A dermoscopic view of a skin lesion — 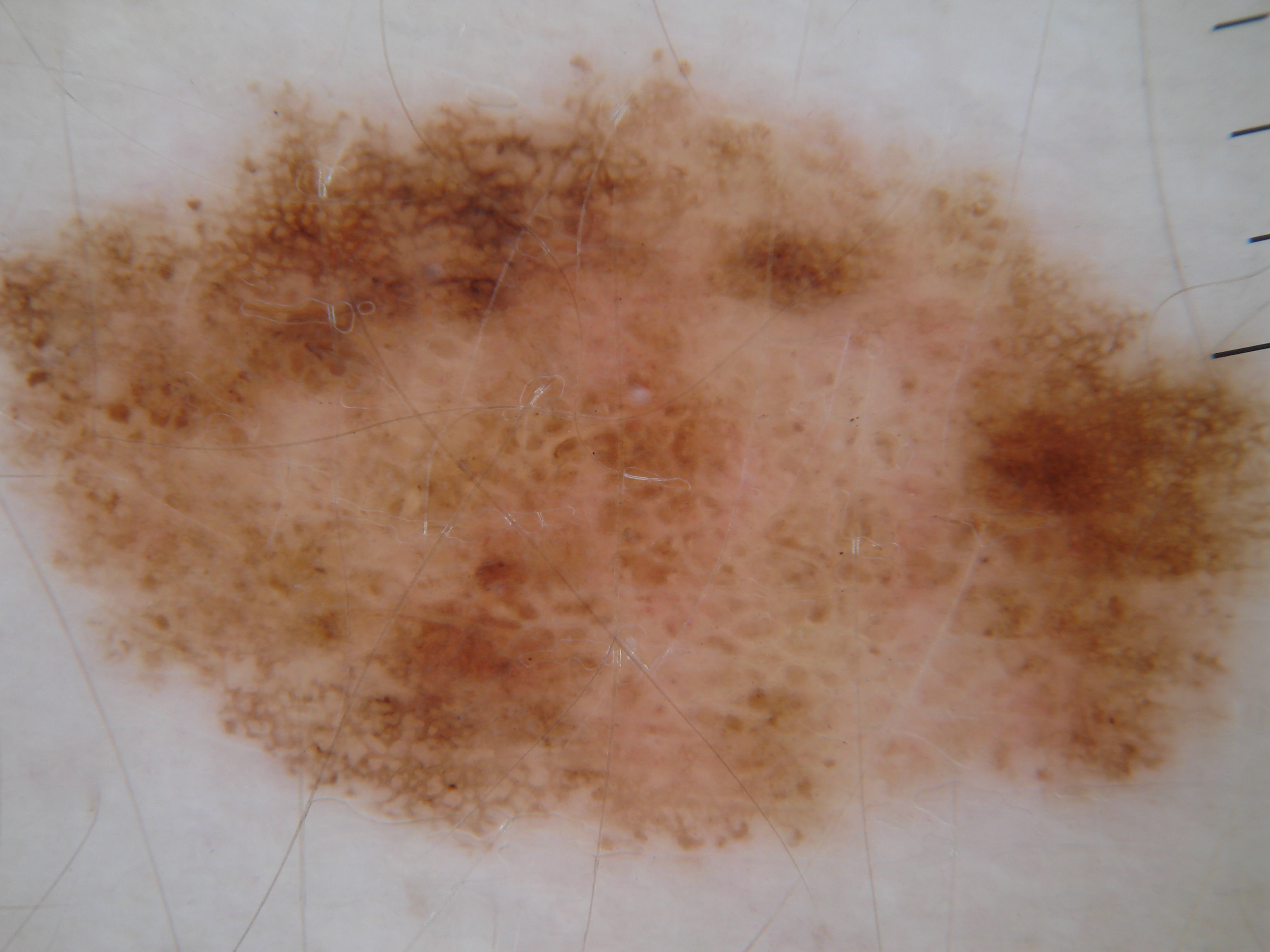{
  "lesion_location": {
    "bbox_xyxy": [
      2,
      45,
      1269,
      862
    ]
  },
  "diagnosis": {
    "name": "melanocytic nevus",
    "malignancy": "benign",
    "lineage": "melanocytic",
    "provenance": "clinical"
  }
}